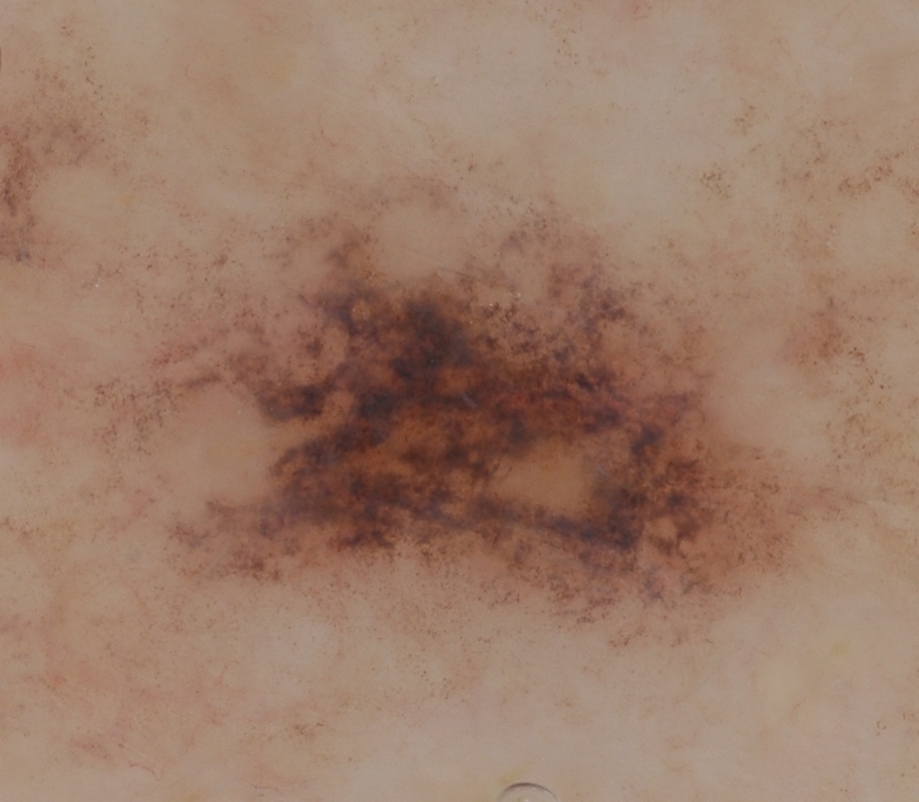A dermatoscopic image of a skin lesion.
Dermoscopically, the lesion shows no negative network, streaks, pigment network, globules, or milia-like cysts.
The lesion extends across almost the whole field of view.
Histopathological examination showed a melanoma.